Fitzpatrick II. The photograph is a close-up of the affected area: 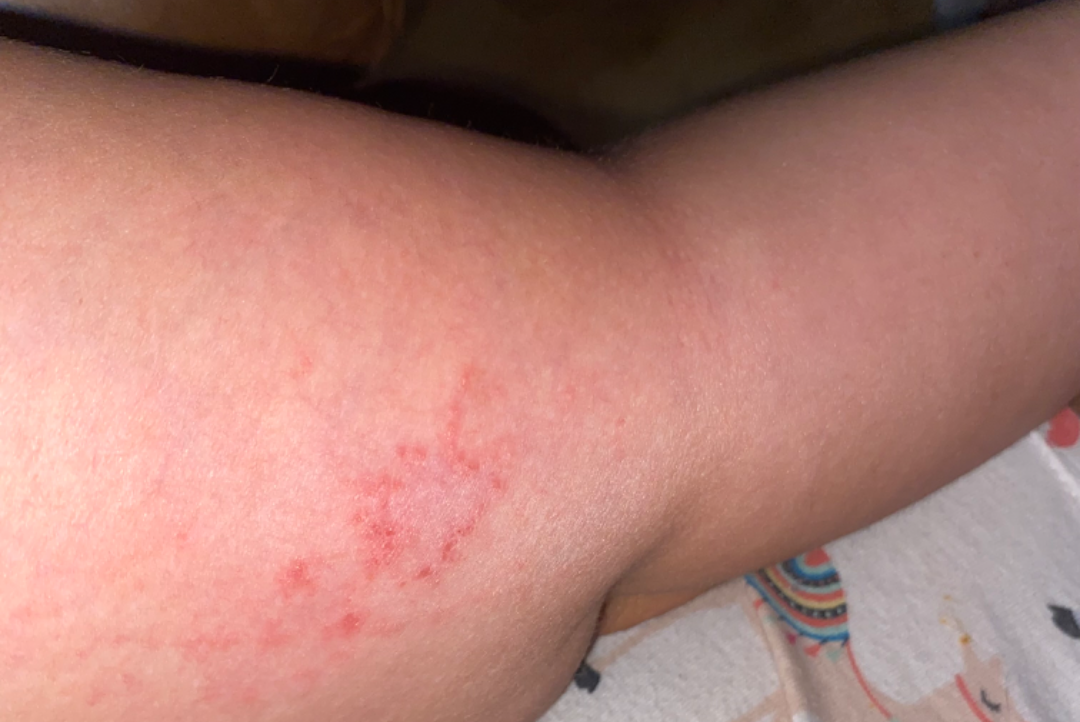Impression:
Diagnostic features were not clearly distinguishable in this photograph.